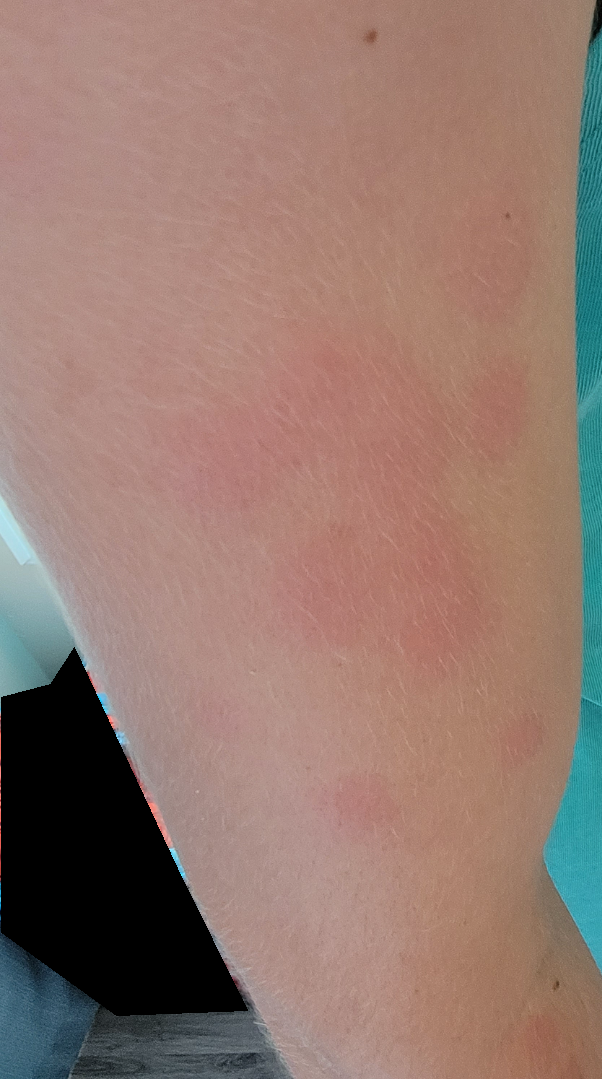Most consistent with Urticaria.